The photograph was taken at a distance: 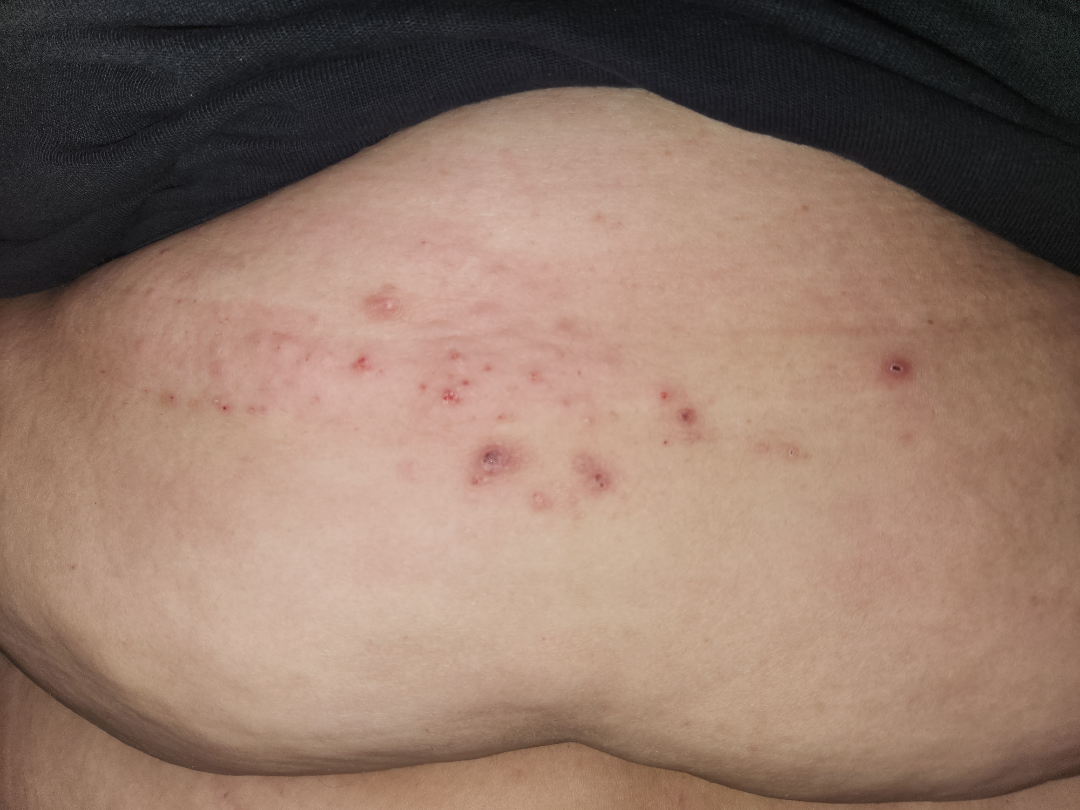differential: Allergic Contact Dermatitis